A skin lesion imaged with a dermatoscope.
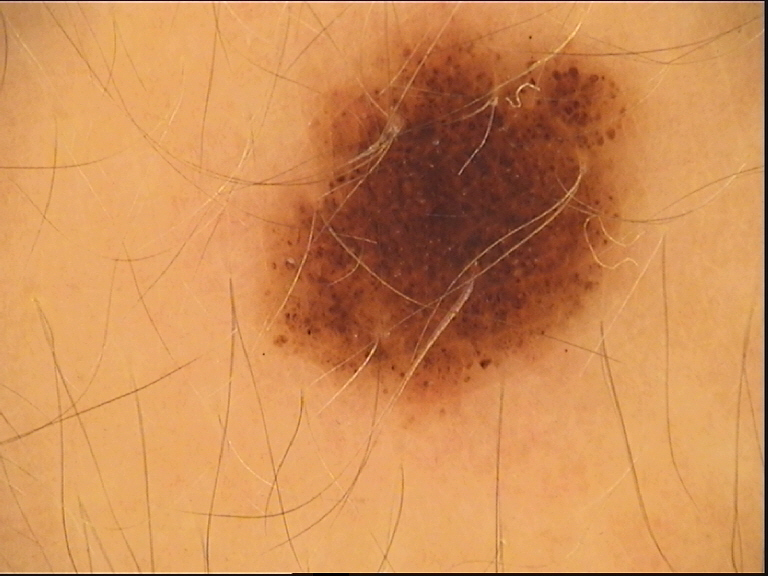Findings:
- class — compound nevus (expert consensus)